The lesion involves the head or neck and back of the torso; female patient, age 30–39; this image was taken at an angle — 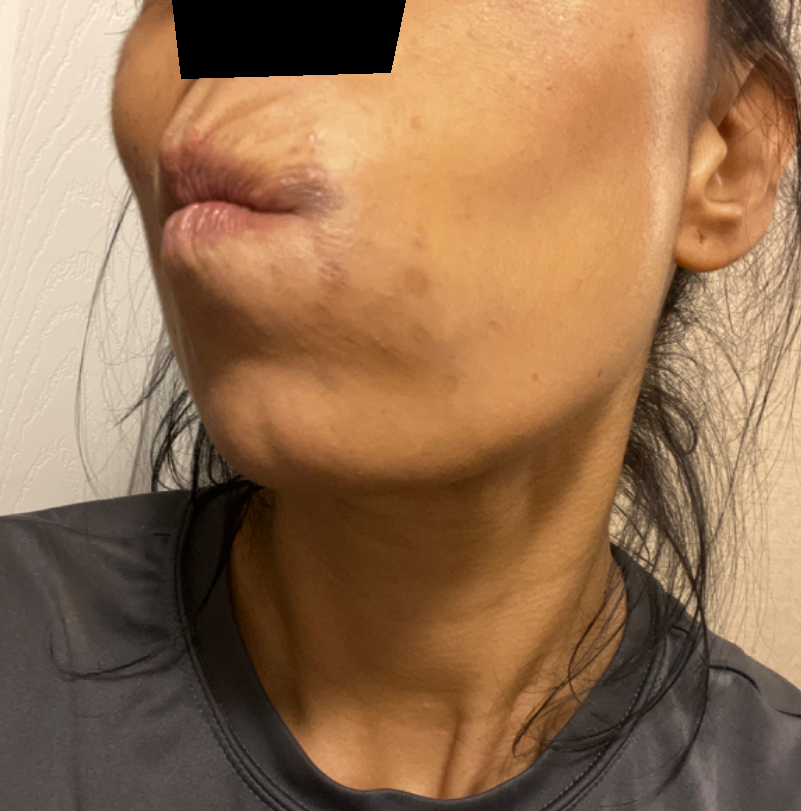Clinical context: No constitutional symptoms were reported. The patient described the issue as a rash. Present for one to three months. Symptoms reported: bothersome appearance. Assessment: On photographic review, most consistent with Perioral Dermatitis; with consideration of Acne.